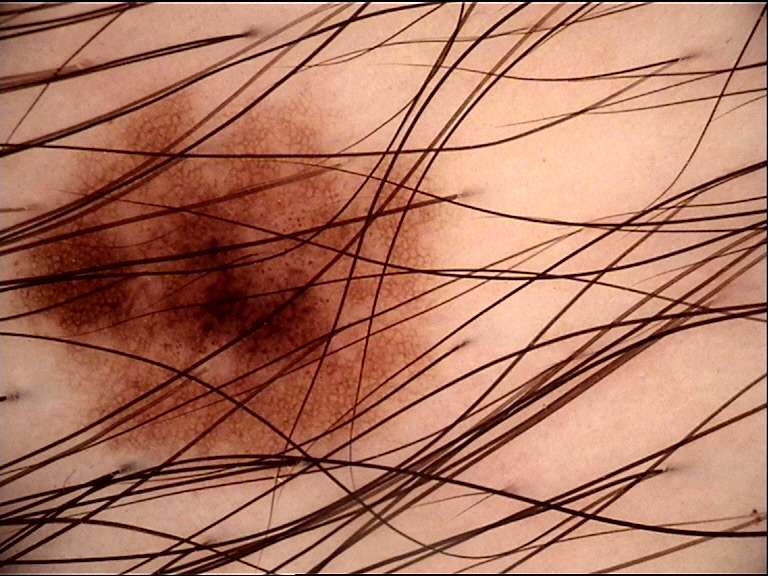label: dysplastic junctional nevus (expert consensus).